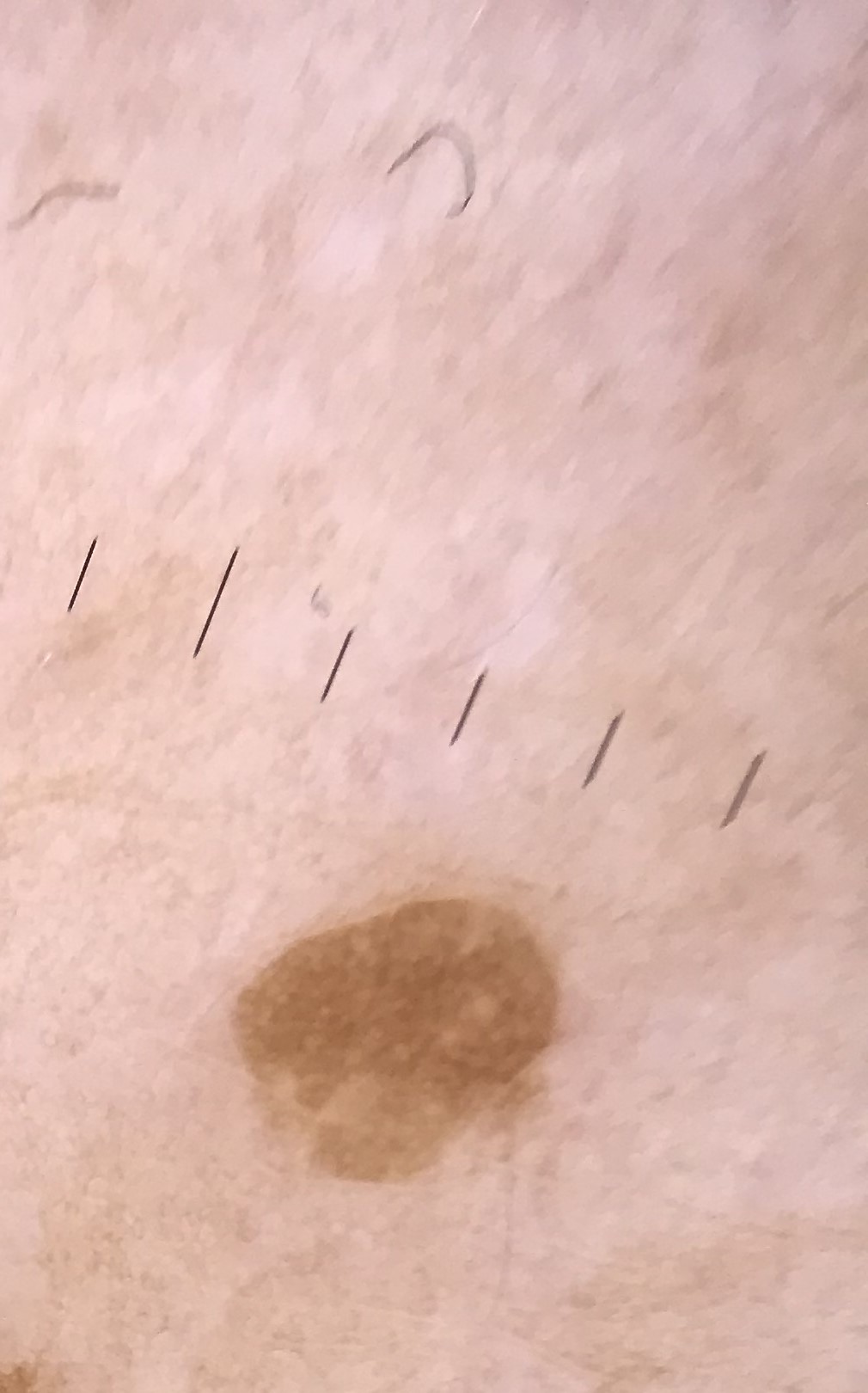Q: What is the imaging modality?
A: dermoscopy
Q: What kind of lesion is this?
A: keratinocytic
Q: What is this lesion?
A: seborrheic keratosis (expert consensus)